A smartphone photograph of a skin lesion · a male subject in their 60s.
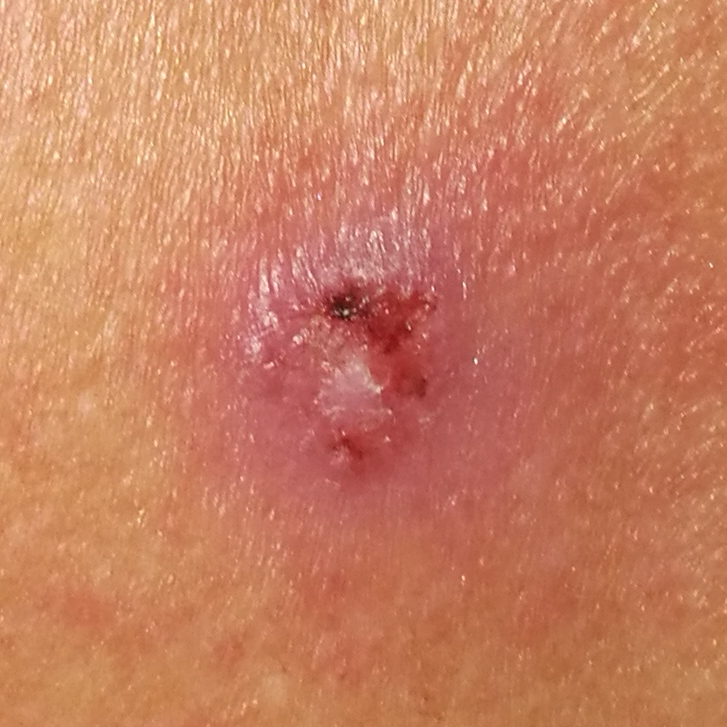  lesion_location: the back
  symptoms:
    present:
      - itching
      - bleeding
      - pain
      - elevation
    absent:
      - change in appearance
      - growth
  diagnosis:
    name: basal cell carcinoma
    code: BCC
    malignancy: malignant
    confirmation: histopathology